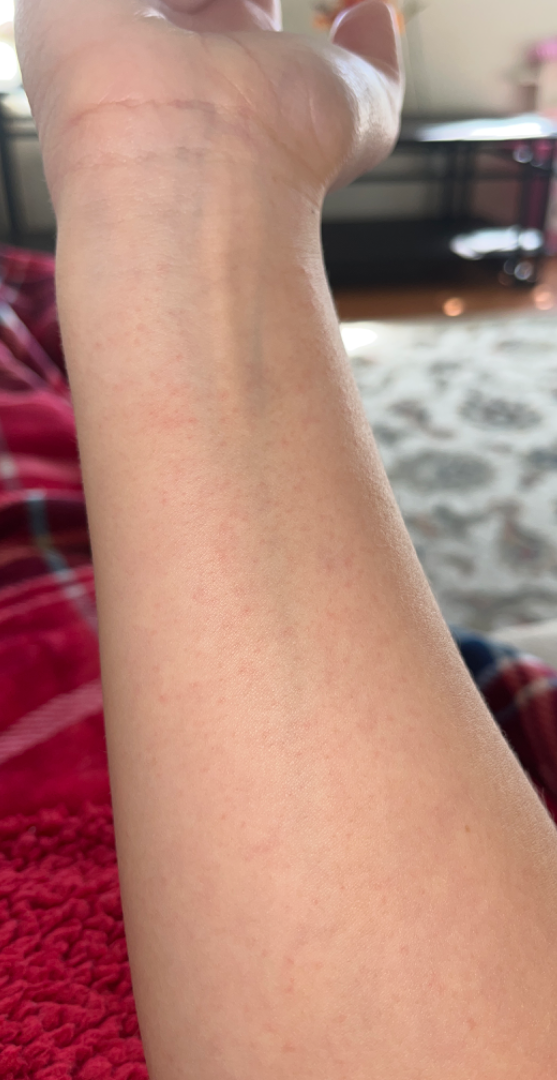diagnostic considerations = most consistent with Irritant Contact Dermatitis.